A smartphone photograph of a skin lesion. A female subject aged 49: 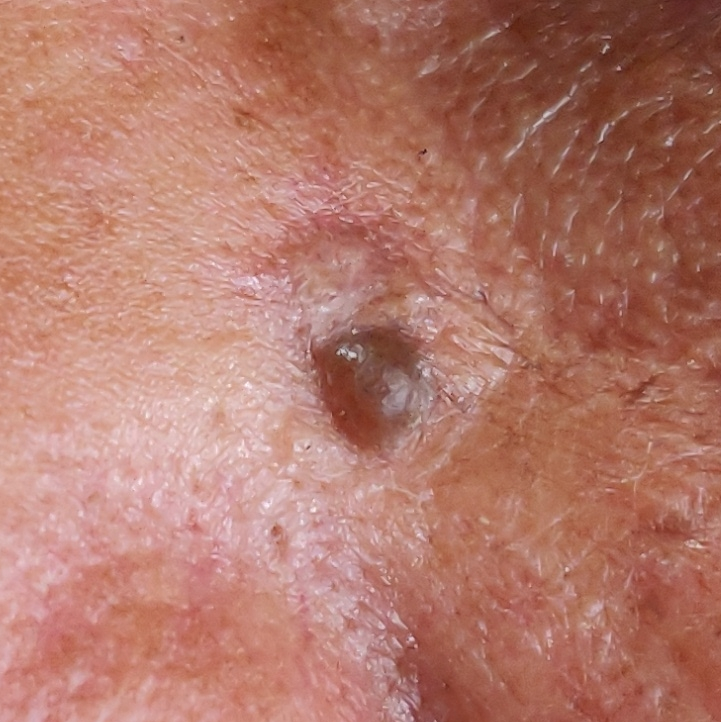The lesion involves the nose.
Histopathology confirmed a basal cell carcinoma.